A female patient aged 65; a clinical close-up photograph of a skin lesion: 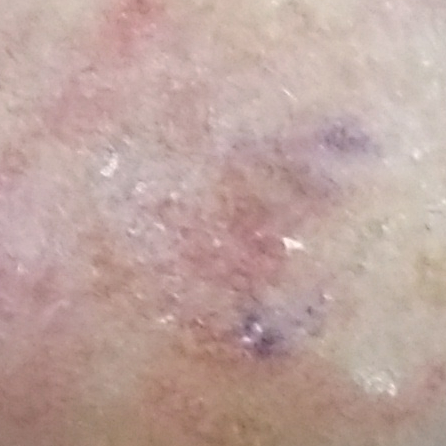<skin_lesion>
  <lesion_location>the nose</lesion_location>
  <symptoms>
    <absent>change in appearance</absent>
  </symptoms>
  <diagnosis>
    <name>actinic keratosis</name>
    <code>ACK</code>
    <malignancy>indeterminate</malignancy>
    <confirmation>histopathology</confirmation>
  </diagnosis>
</skin_lesion>